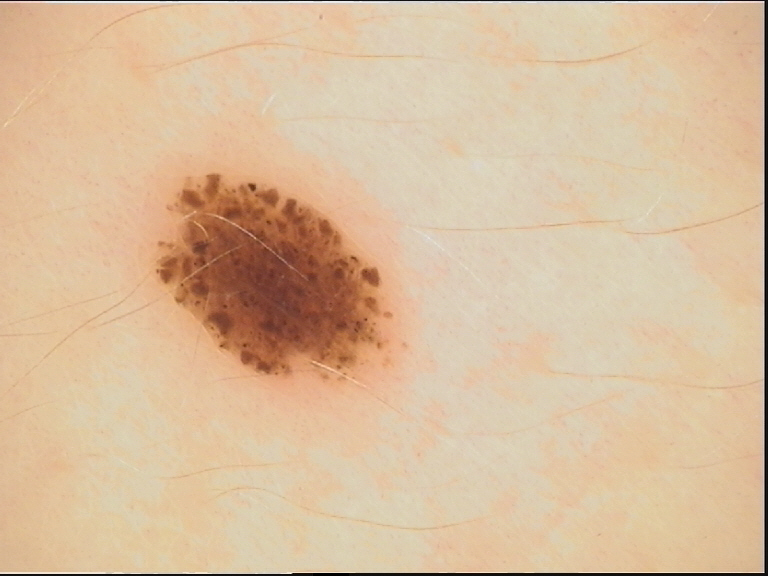Consistent with a dysplastic junctional nevus.